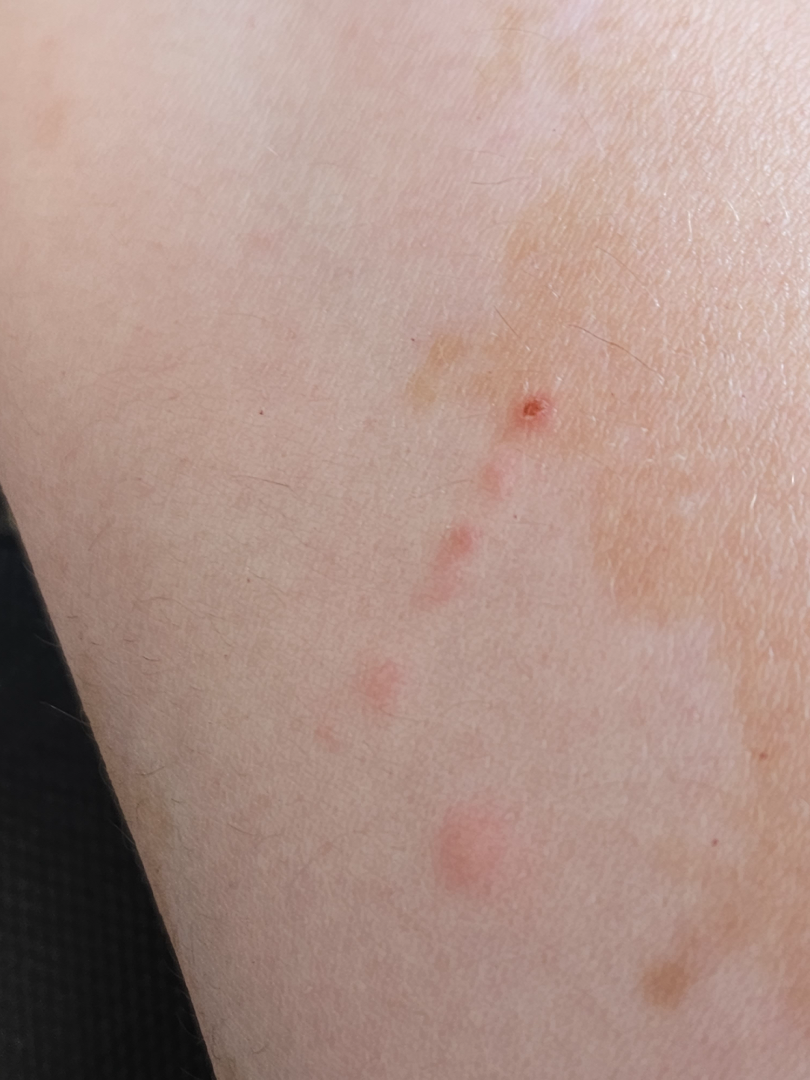image framing — close-up
surface texture — raised or bumpy
patient — female, age 40–49
affected area — arm
skin tone — Fitzpatrick phototype I
symptom duration — less than one week